The subject is a male aged 40–49; the affected area is the head or neck; close-up view — 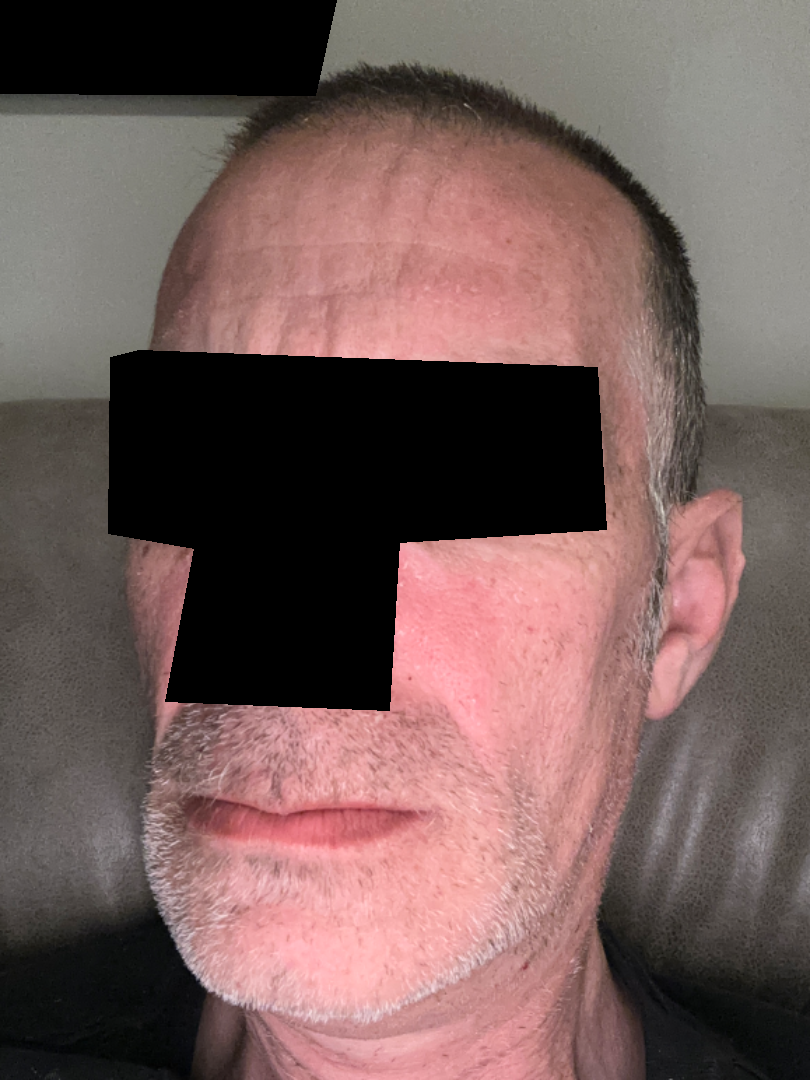No clear dermatological pathology was apparent in the photograph.